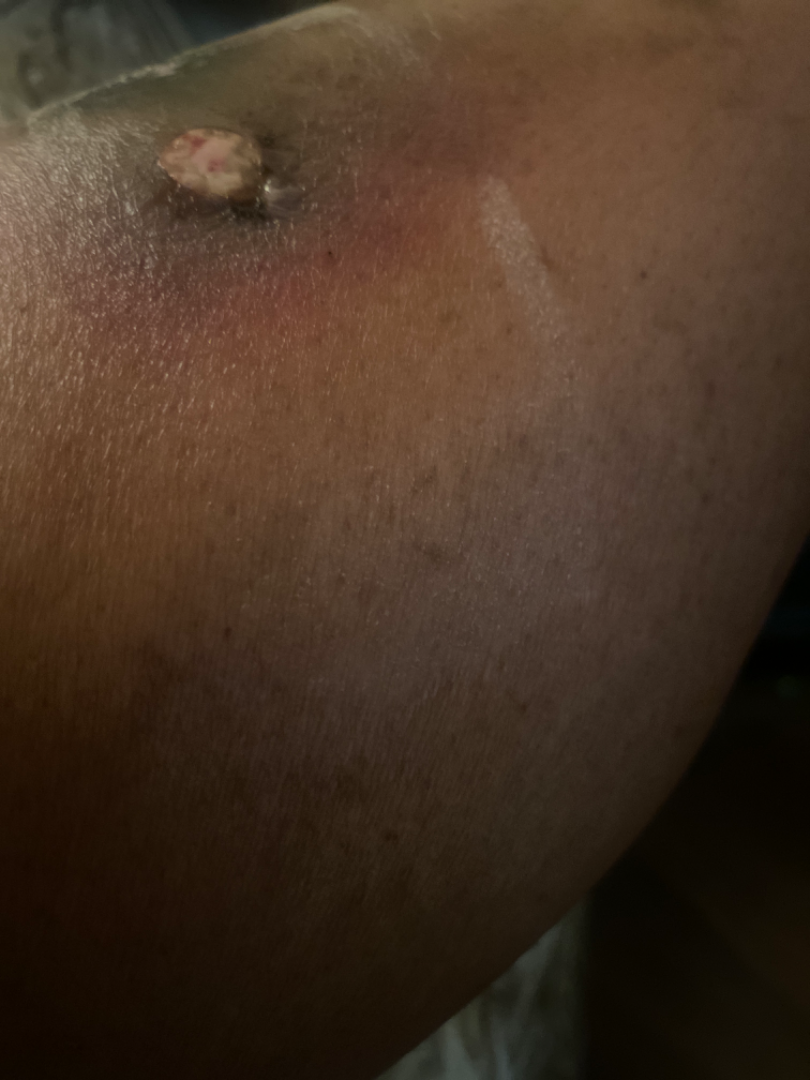assessment = indeterminate from the photograph, self-categorized as = a rash, texture = flat, anatomic site = leg, present for = one to four weeks, shot type = at an angle.